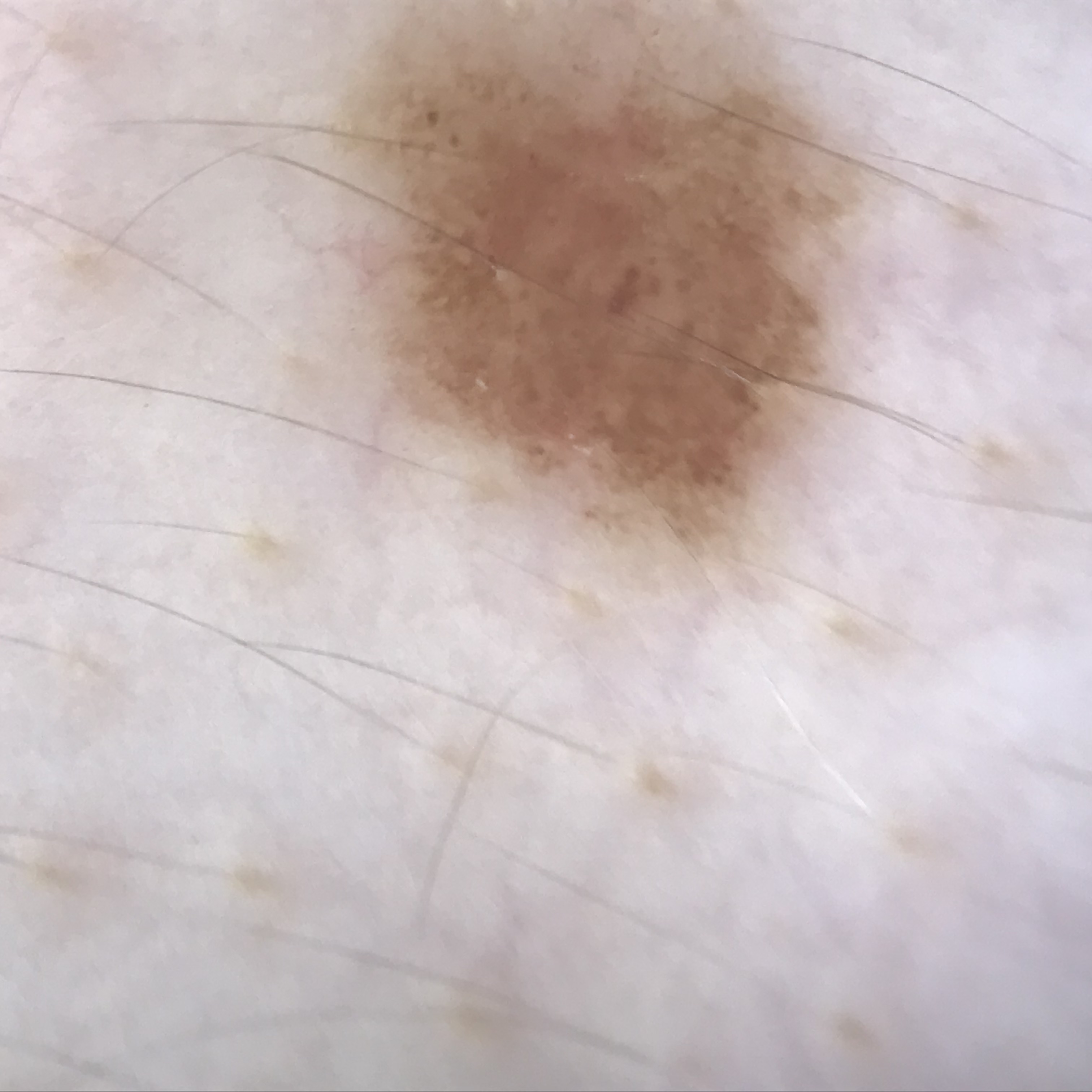Summary: A dermoscopic image of a skin lesion. Impression: Labeled as a benign lesion — a dysplastic junctional nevus.